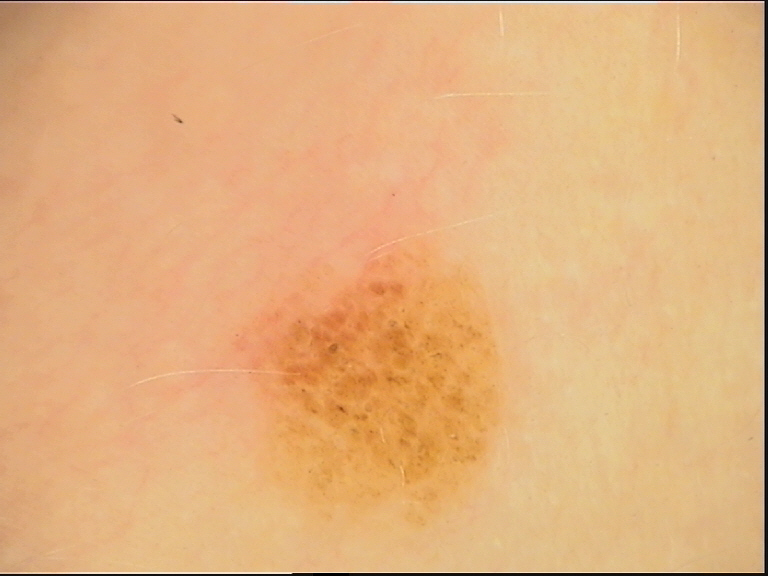Conclusion: The diagnostic label was a dysplastic compound nevus.